A dermoscopy image of a single skin lesion.
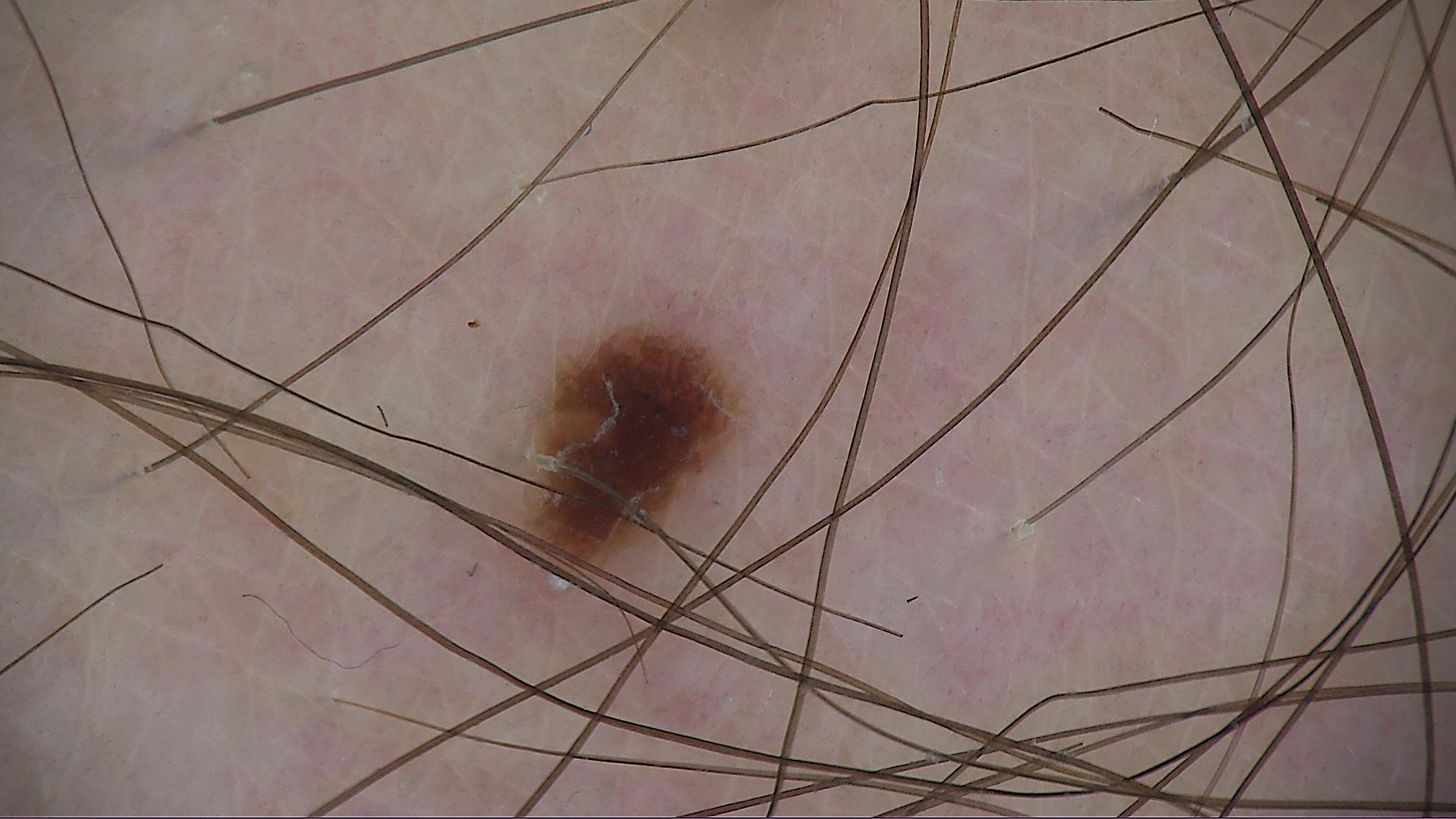Diagnosed as a banal lesion — a junctional nevus.